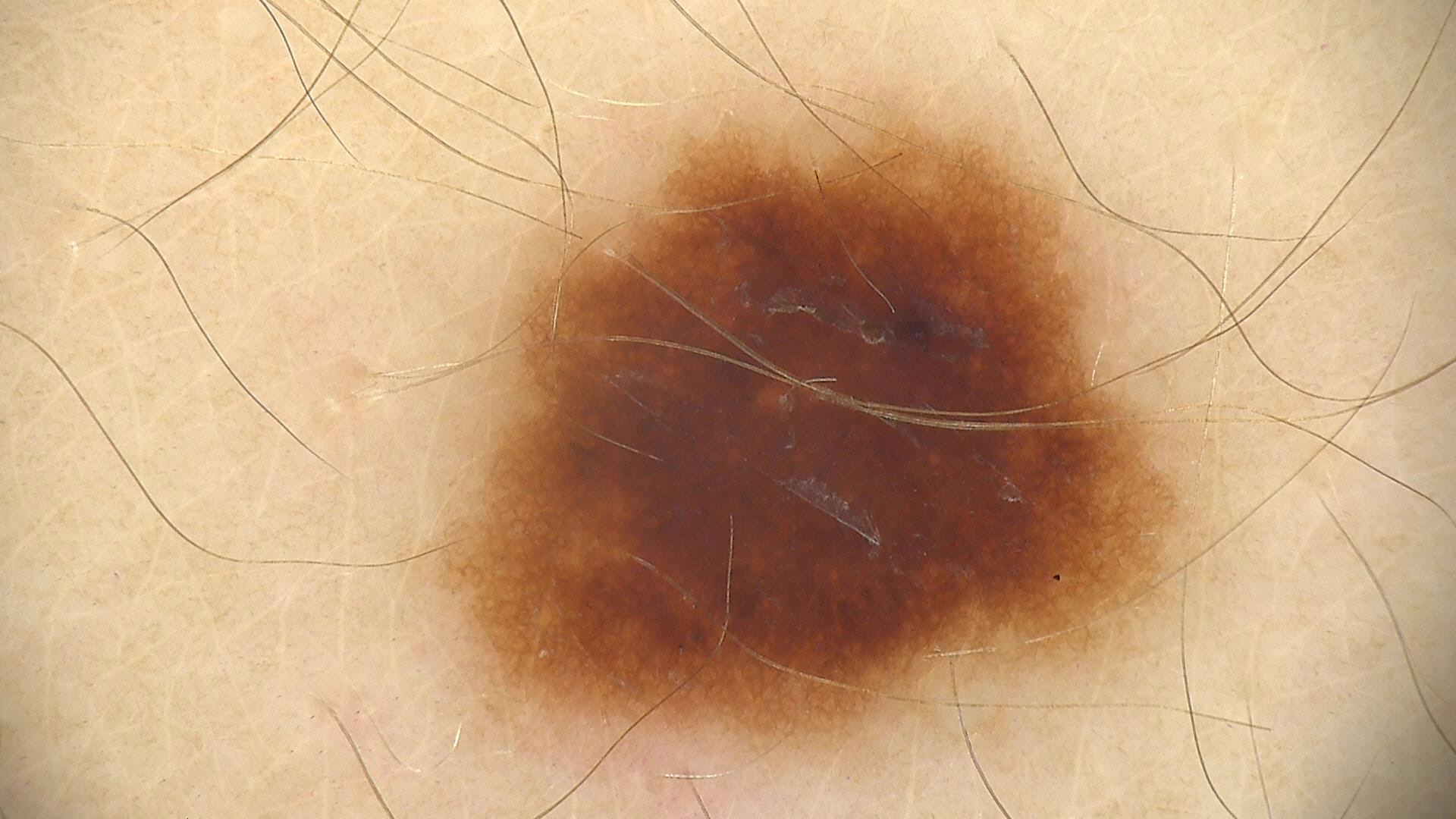diagnostic label — dysplastic junctional nevus (expert consensus).